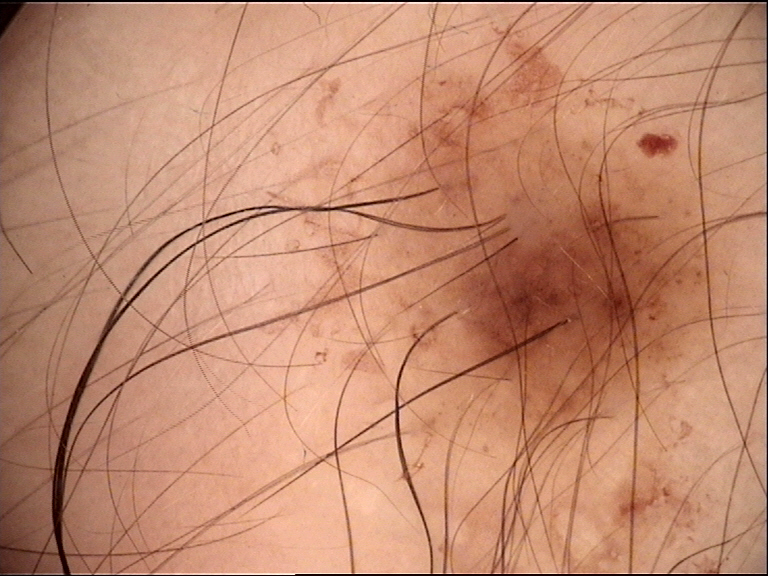class: congenital compound nevus (expert consensus).